Reported lesion symptoms include pain · the patient reports the condition has been present for less than one week · the photograph is a close-up of the affected area · female patient, age 70–79 · texture is reported as raised or bumpy · the patient considered this a rash · no constitutional symptoms were reported · the affected area is the back of the torso:
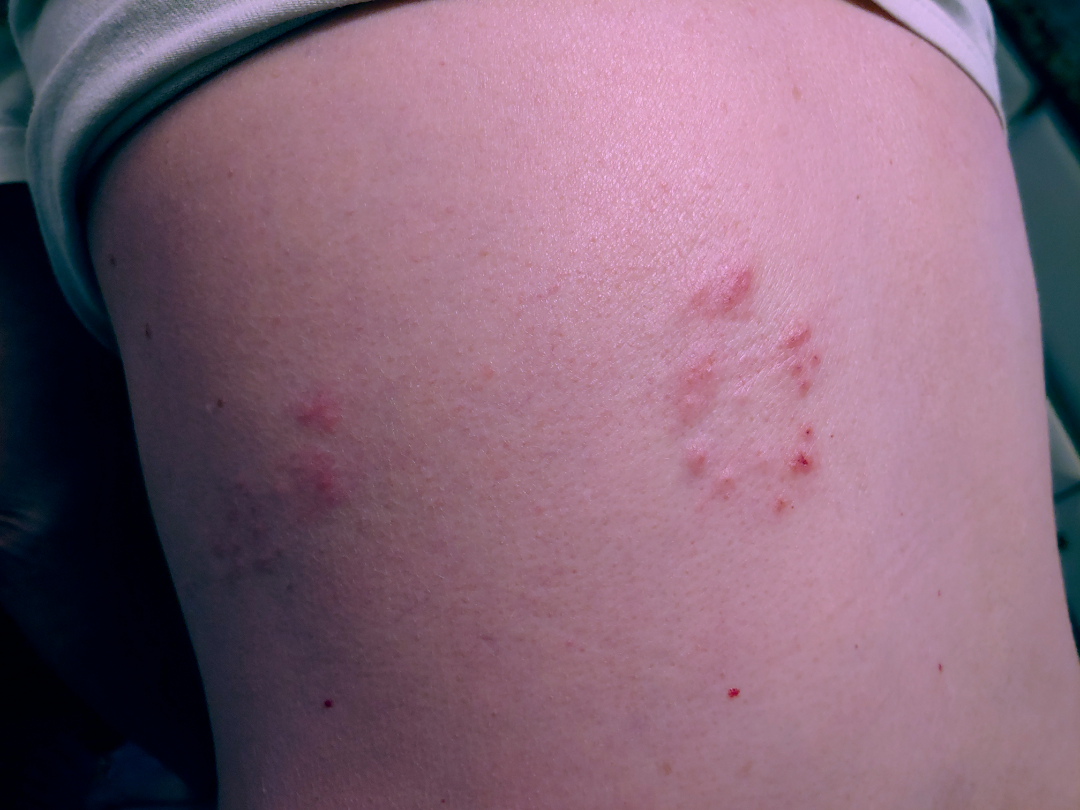The image was not sufficient for the reviewer to characterize the skin condition.